The subject is a female aged 30–39 · close-up view: 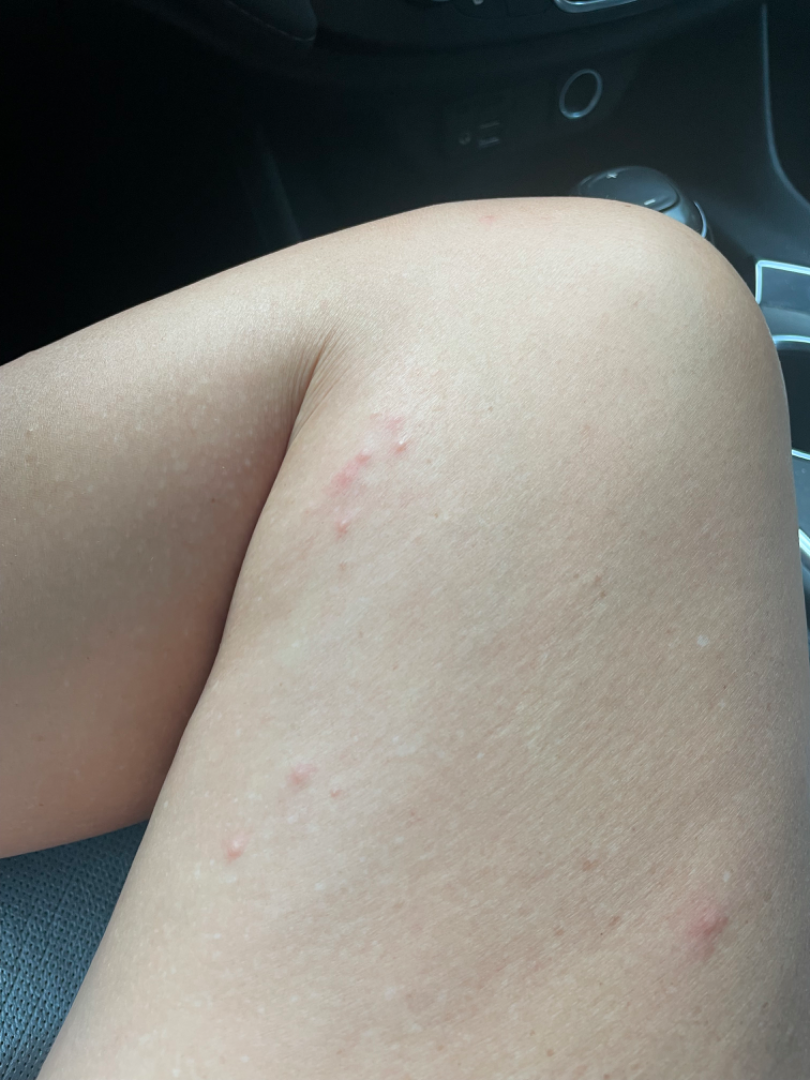• symptoms: itching
• associated systemic symptoms: none reported
• duration: less than one week
• described texture: raised or bumpy
• differential diagnosis: Folliculitis, Insect Bite and Molluscum Contagiosum were each considered, in no particular order